This is a close-up image. The affected area is the leg: 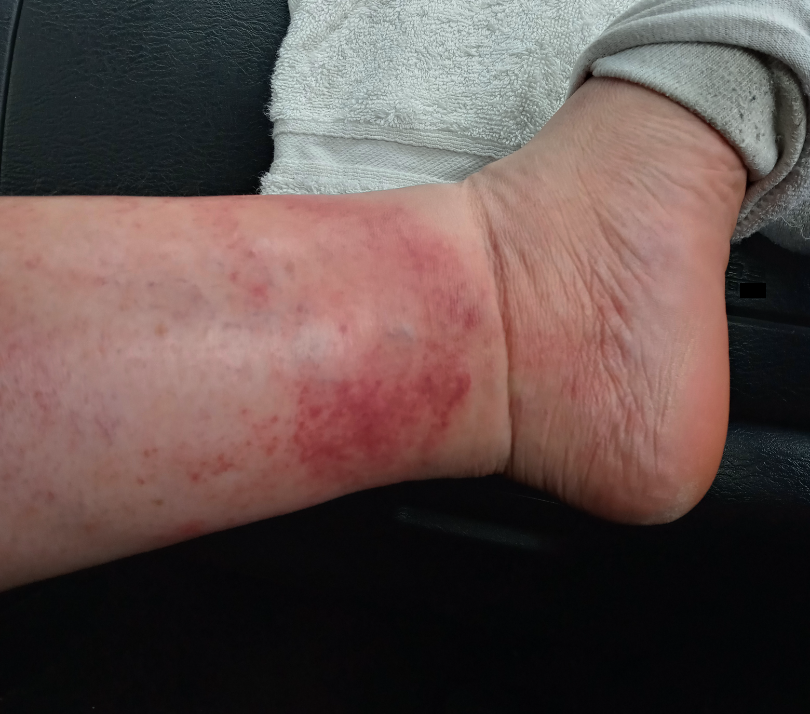clinical impression — three dermatologists independently reviewed the case: favoring Stasis Dermatitis; possibly Pigmented purpuric eruption; less likely is Eczema.